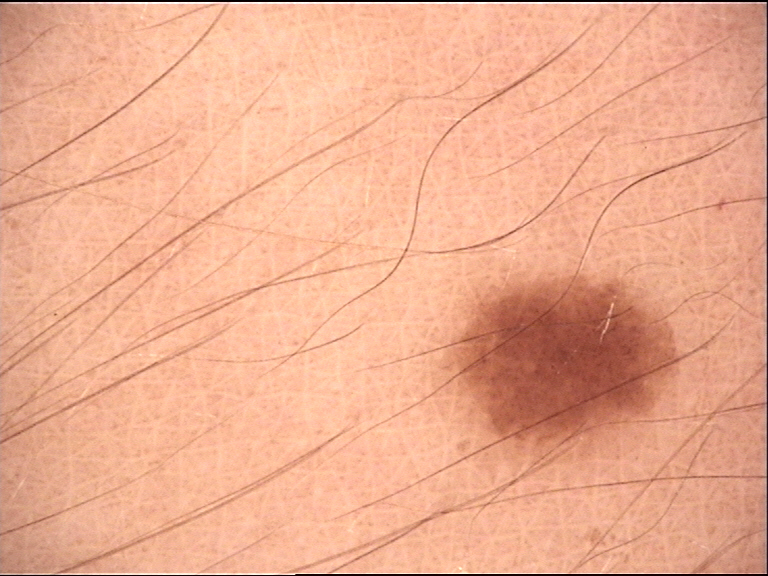Diagnosed as a junctional nevus.